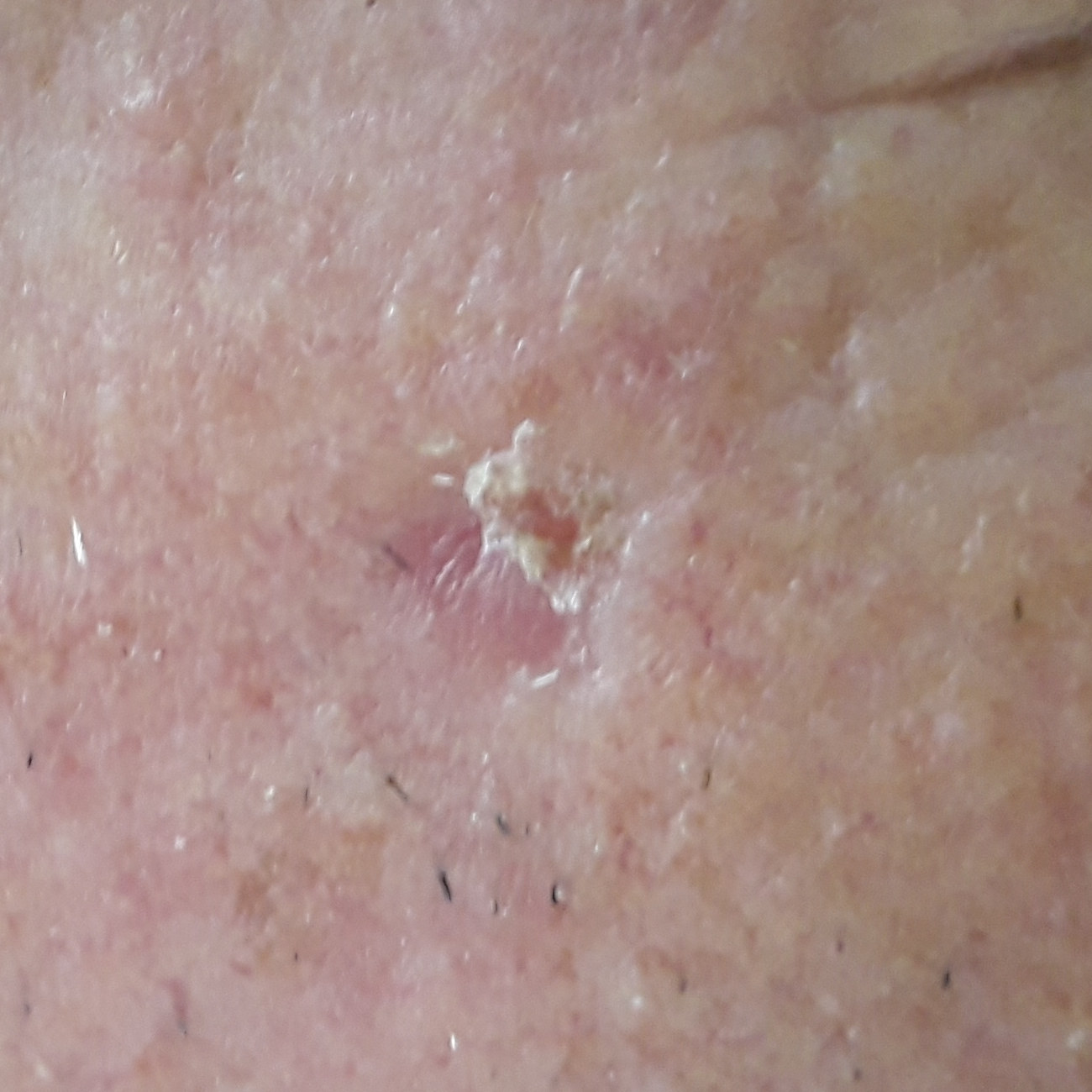The patient was assessed as Fitzpatrick III. A clinical photograph of a skin lesion. The lesion involves the face. Histopathology confirmed a basal cell carcinoma.